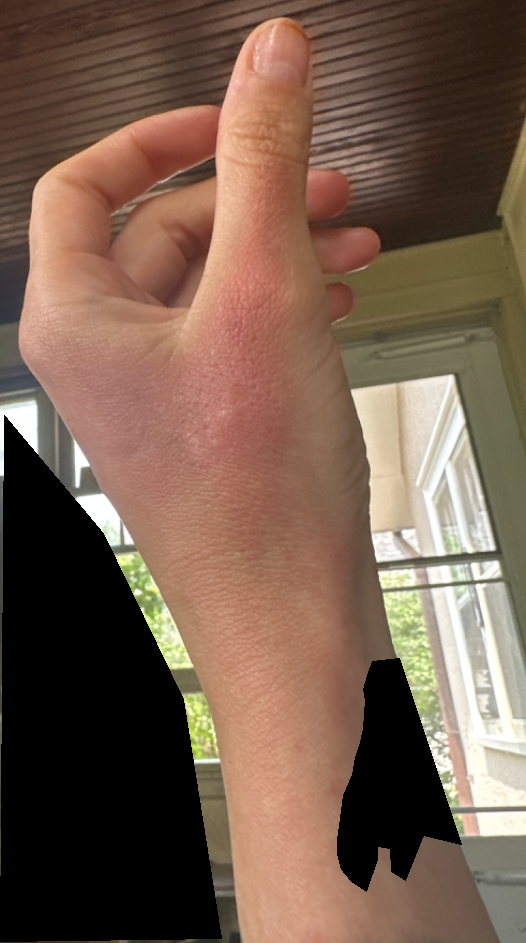Q: Who is the patient?
A: female, age 30–39
Q: Where on the body?
A: back of the hand
Q: What is the framing?
A: at a distance
Q: What is the differential diagnosis?
A: most consistent with Irritant Contact Dermatitis; possibly Allergic Contact Dermatitis